Self-categorized by the patient as a rash. The affected area is the back of the torso. The patient reported no systemic symptoms. An image taken at a distance. The condition has been present for about one day. Female subject, age 40–49. The lesion is associated with burning and itching. The lesion is described as rough or flaky and raised or bumpy.
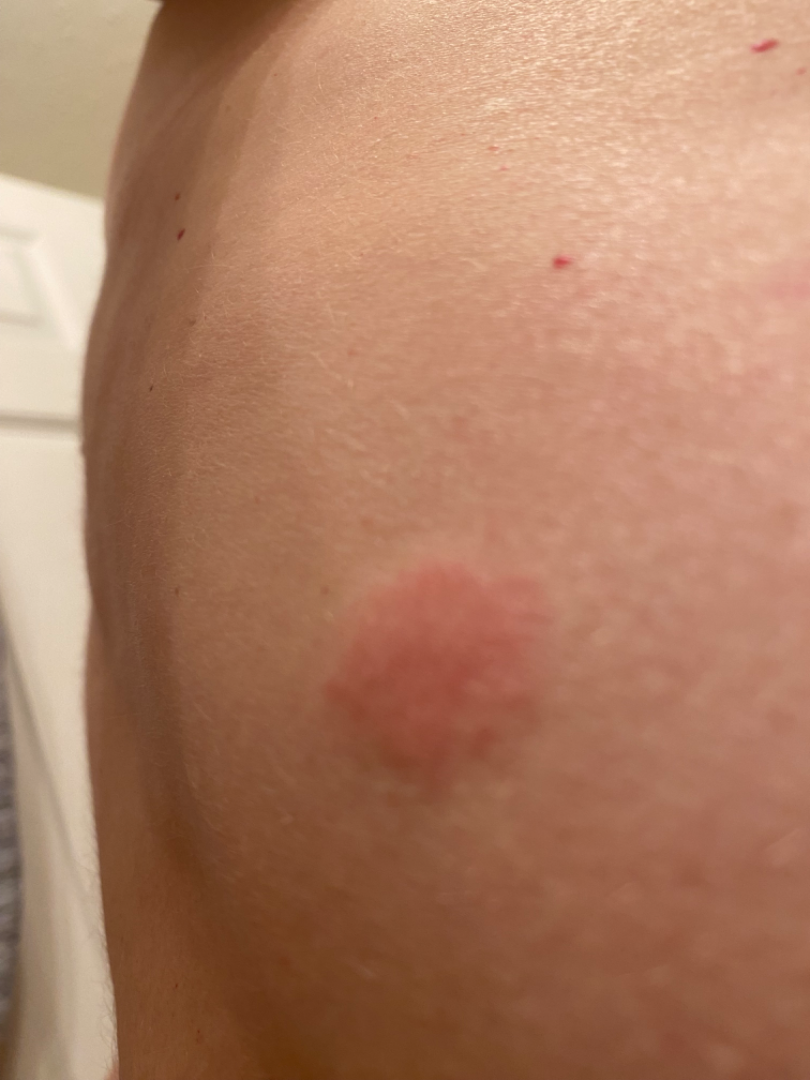Impression:
Insect Bite (52%); Urticaria (26%); Primary cutaneous lymphoma (11%); Cutaneous lupus (11%).